The photograph was taken at a distance; the lesion involves the arm — 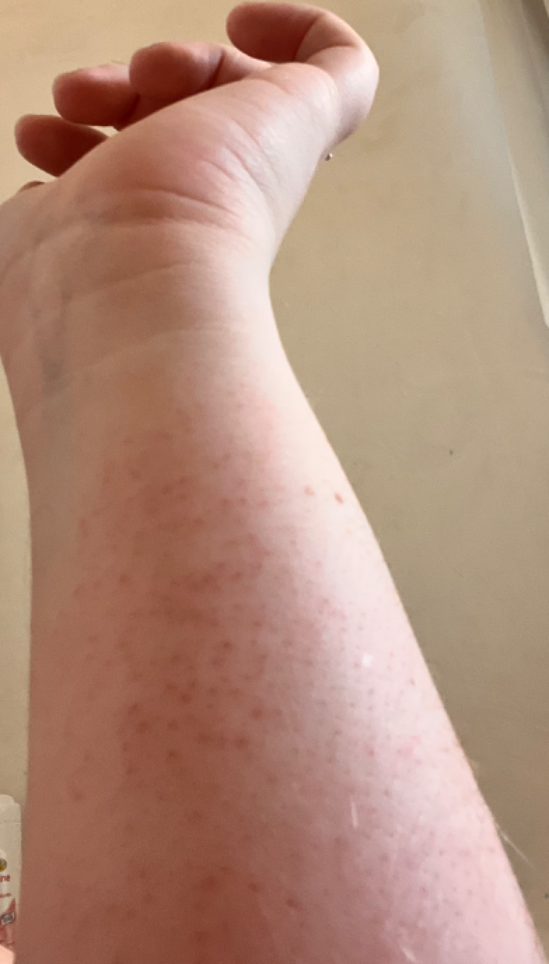impression: most consistent with Keratosis pilaris.